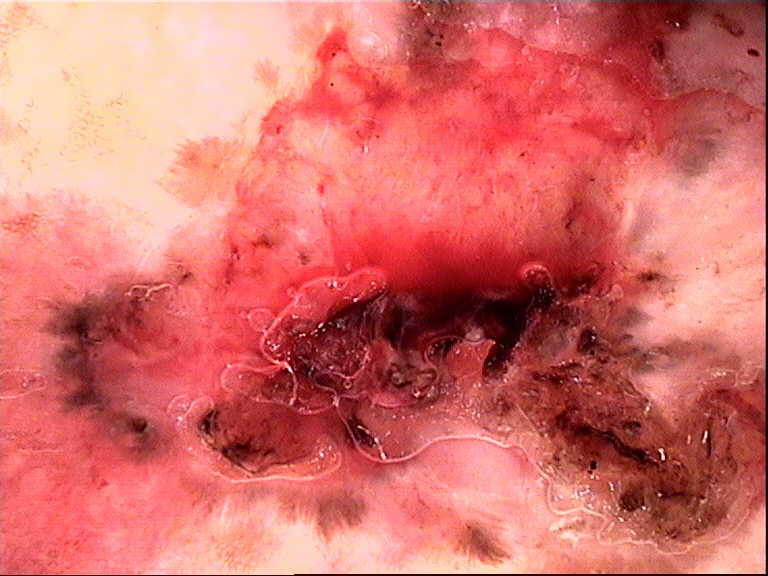{"diagnosis": {"name": "basal cell carcinoma", "code": "bcc", "malignancy": "malignant", "super_class": "non-melanocytic", "confirmation": "histopathology"}}